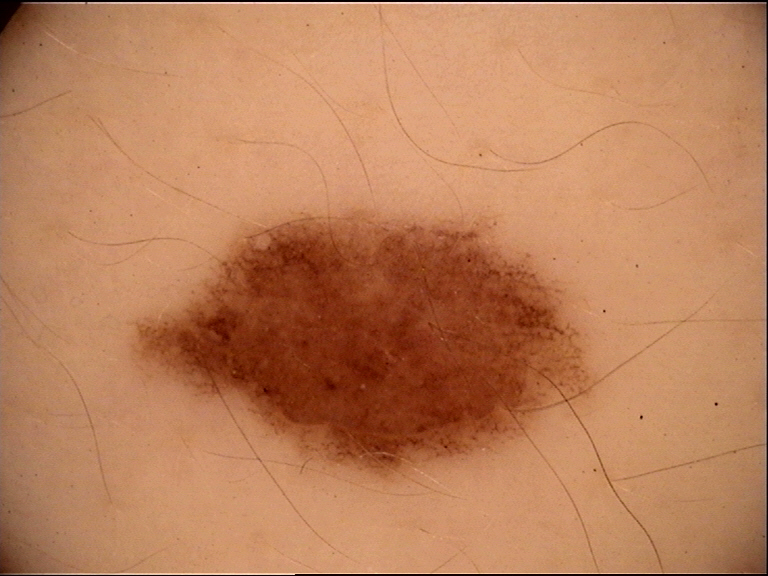Impression:
The diagnostic label was a dysplastic junctional nevus.